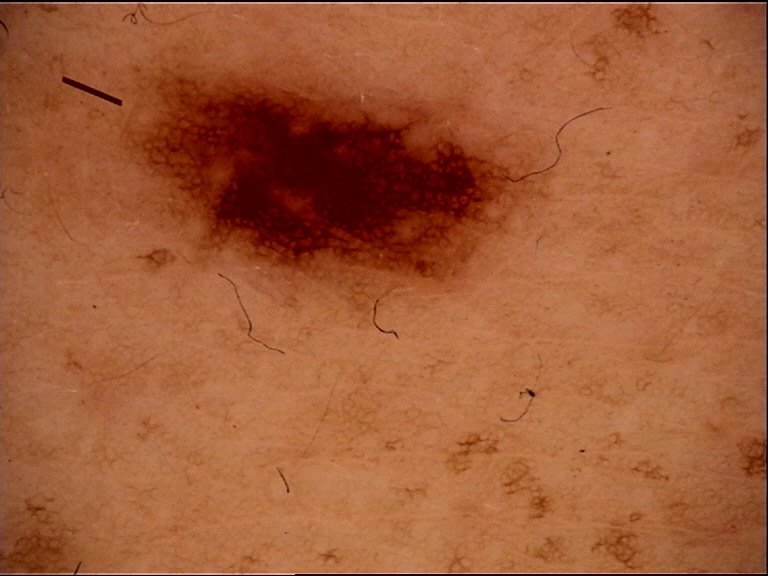Conclusion:
Consistent with a dysplastic junctional nevus.